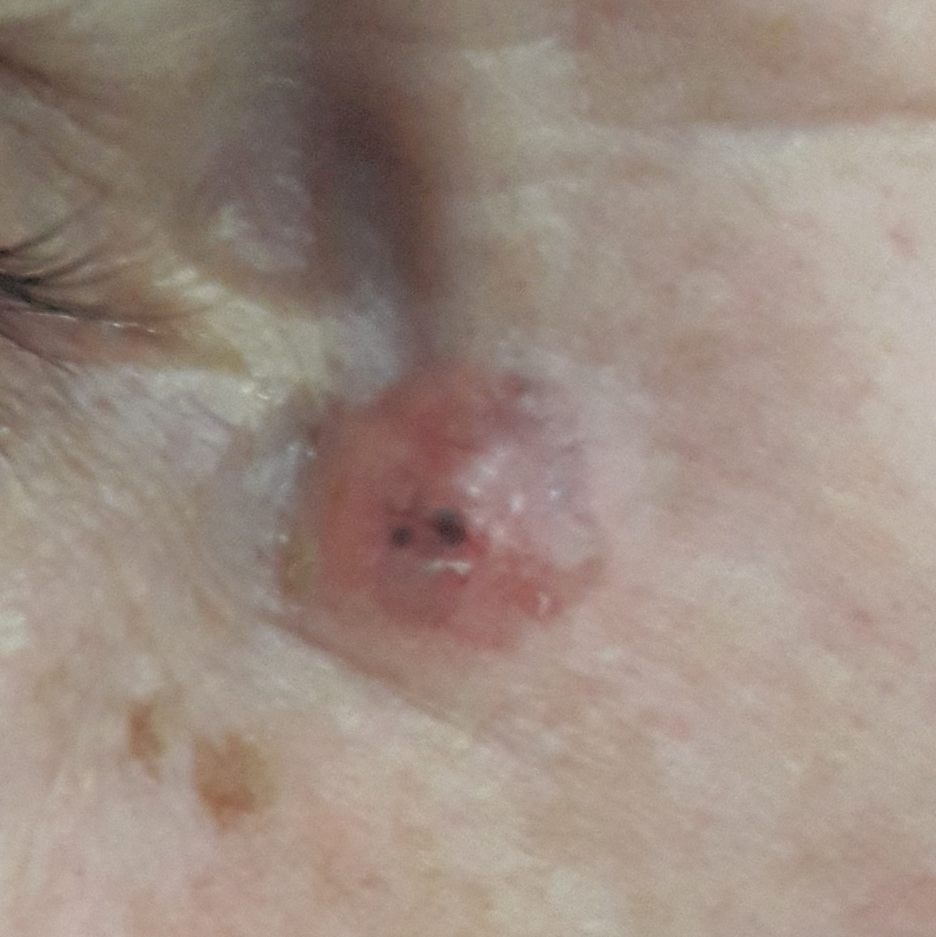patient = female, age 66
skin phototype = II
image type = clinical photograph
exposures = prior malignancy (patient or family), no alcohol use, no pesticide exposure
location = the face
lesion diameter = 7 × 7 mm
patient-reported symptoms = bleeding, growth, itching, elevation
diagnosis = basal cell carcinoma (biopsy-proven)